Dermoscopy of a skin lesion: 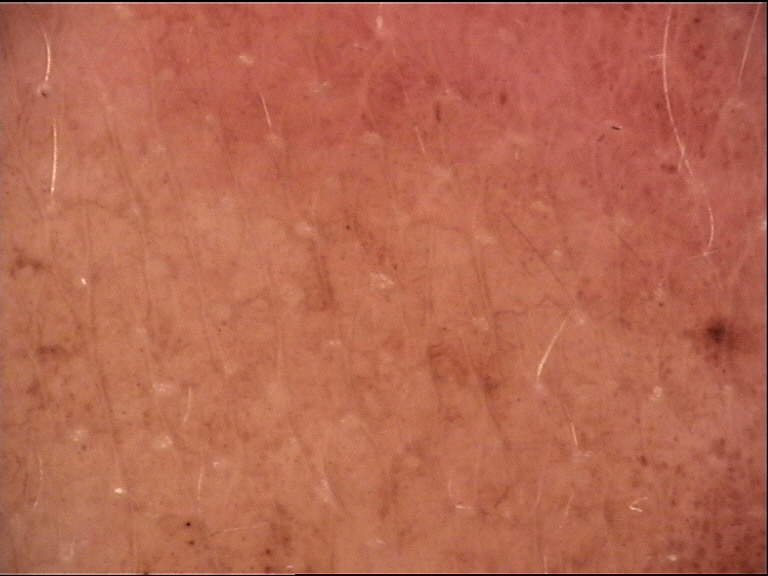* subtype — banal
* label — congenital junctional nevus (expert consensus)